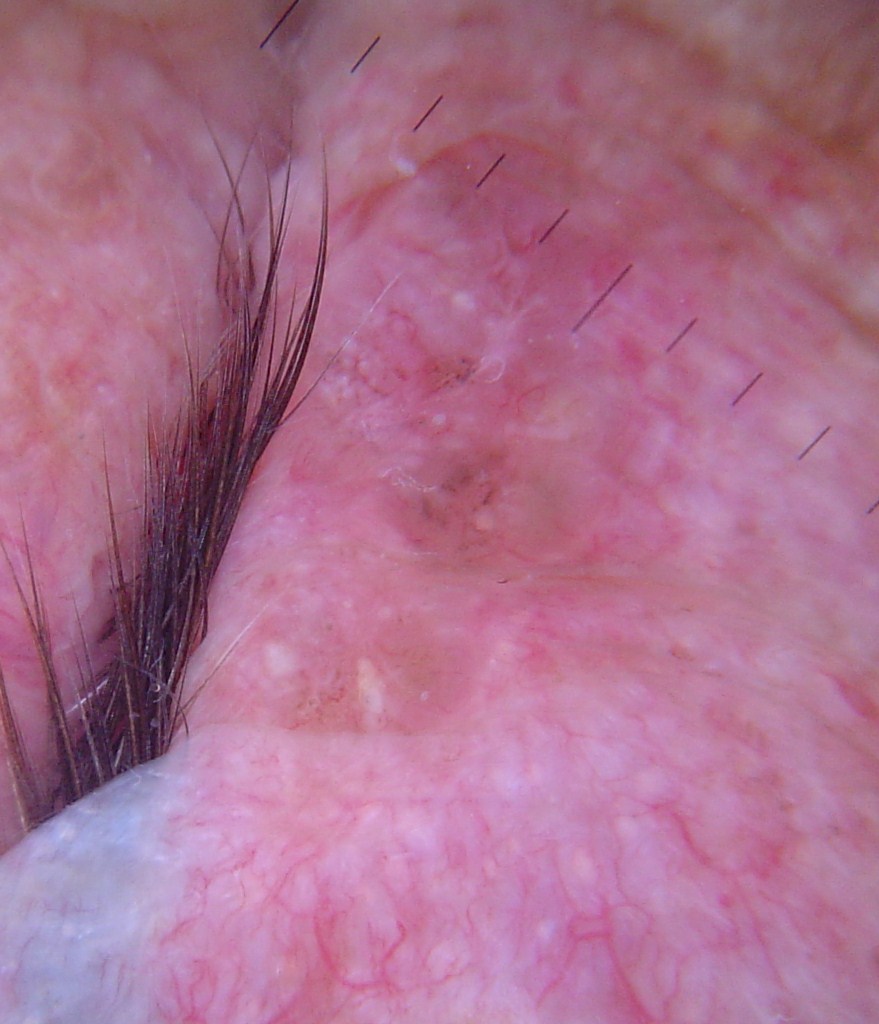modality=dermatoscopy
label=basal cell carcinoma (biopsy-proven)